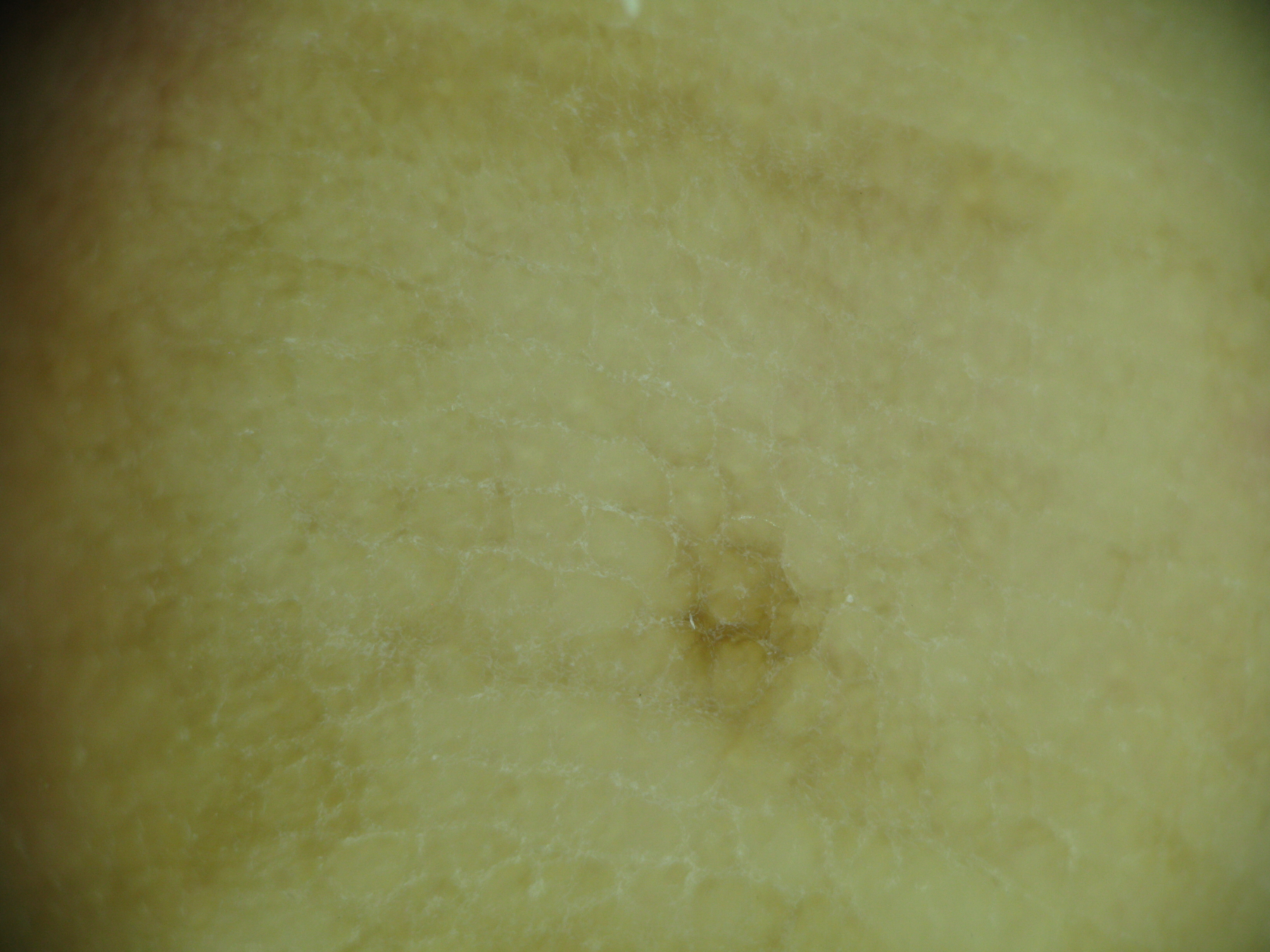Conclusion:
The diagnostic label was a banal lesion — an acral junctional nevus.